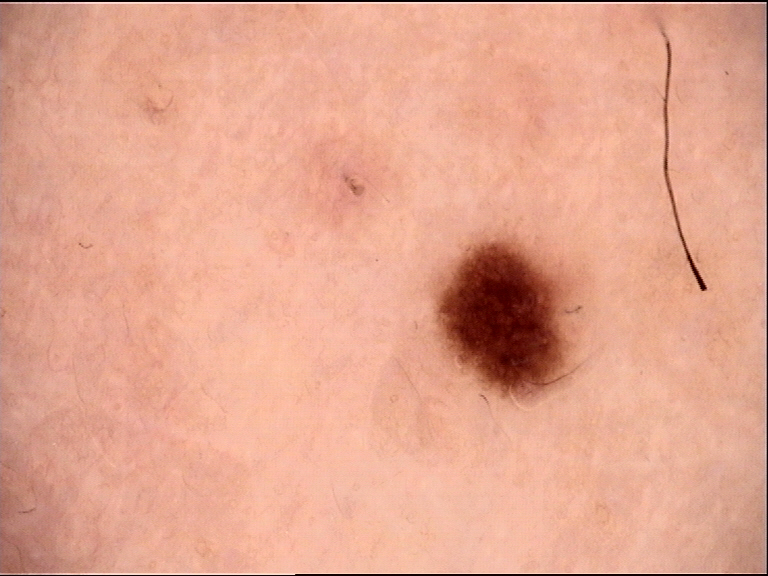classification=banal | assessment=junctional nevus (expert consensus).